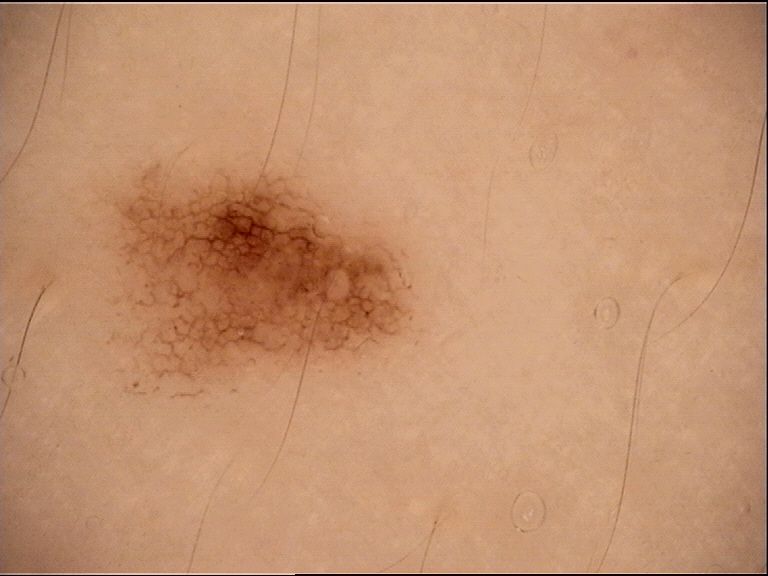modality: dermoscopy | class: dysplastic junctional nevus (expert consensus).